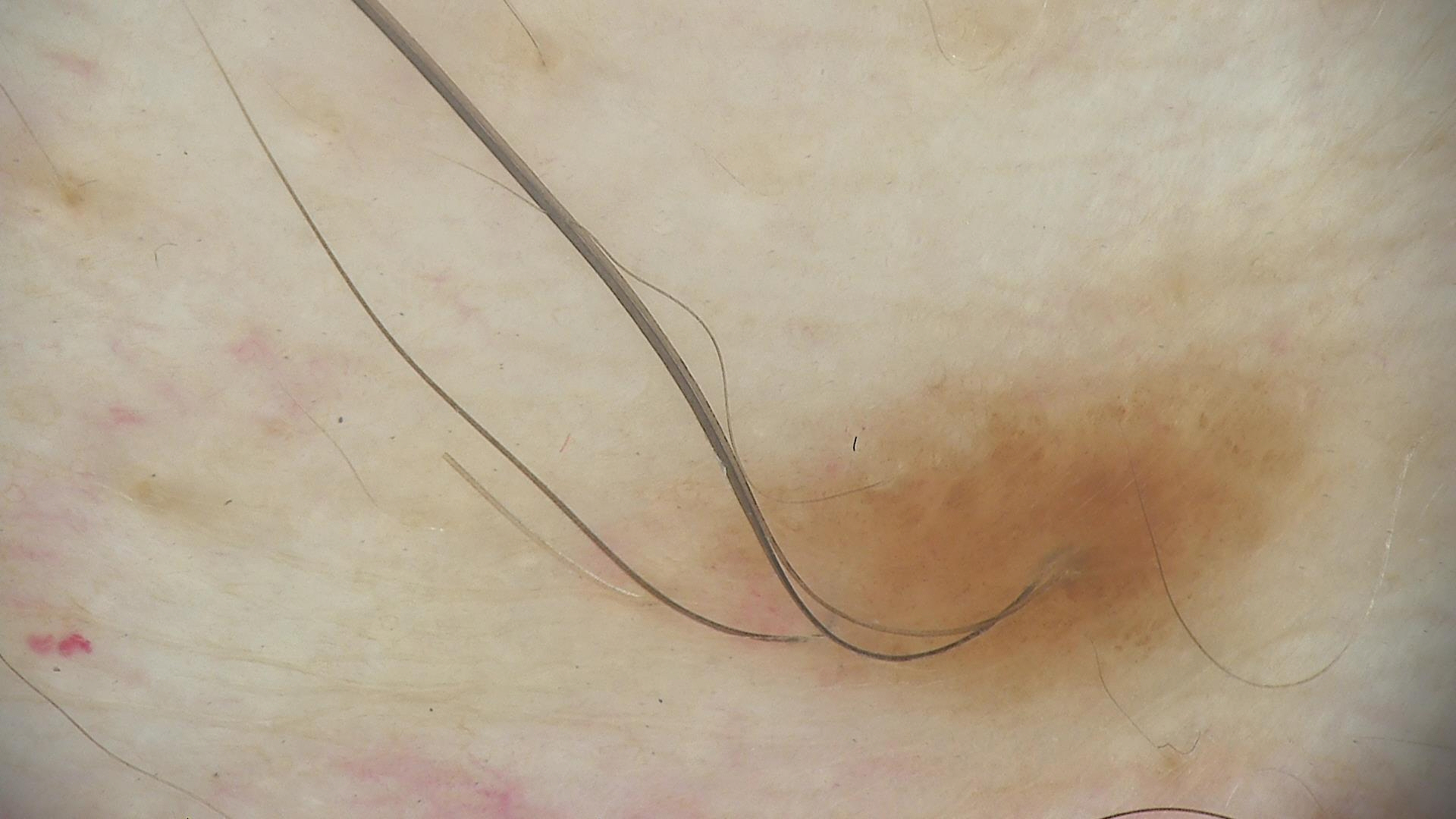Consistent with a compound nevus.